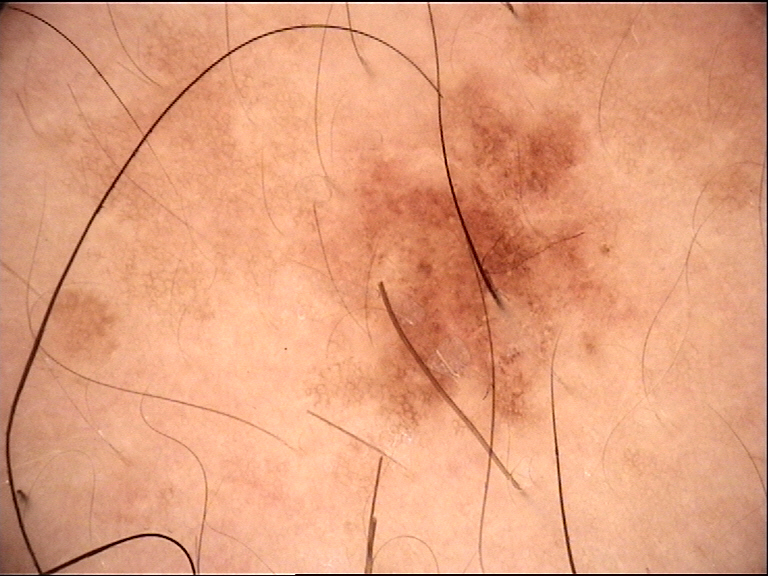A dermoscopy image of a single skin lesion. Consistent with a benign lesion — a dysplastic junctional nevus.